The photo was captured at an angle, the affected area is the sole of the foot.
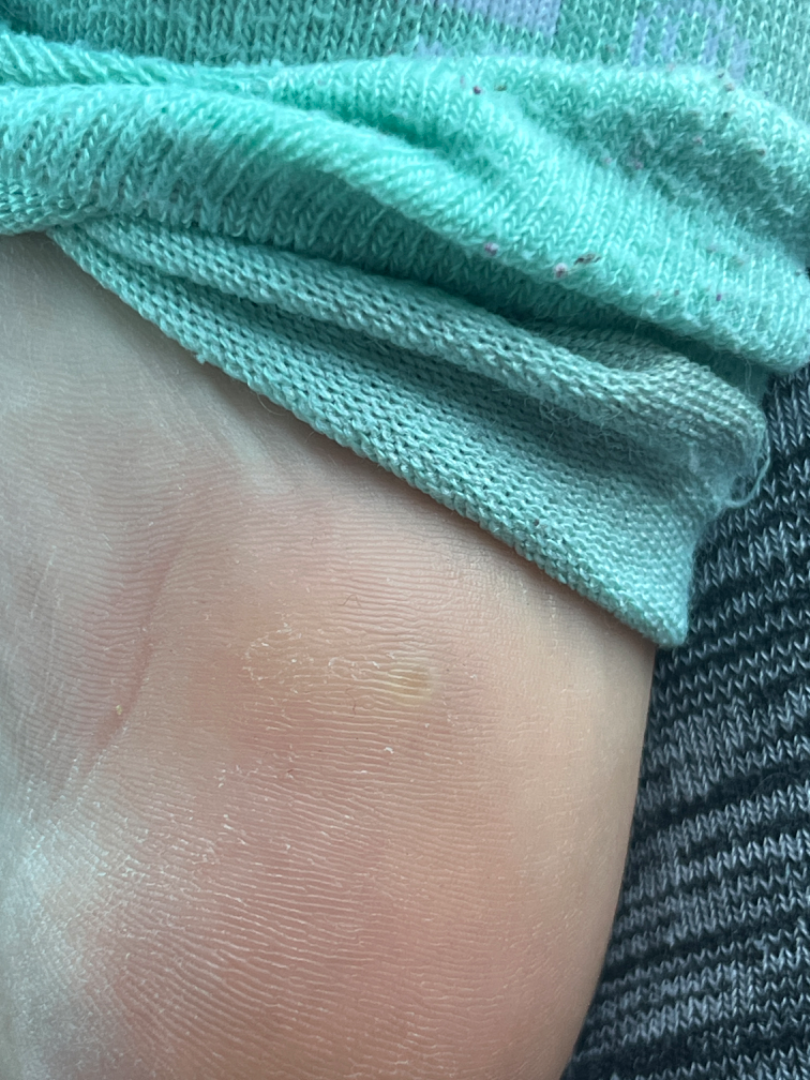Q: Reported symptoms?
A: pain
Q: What is the lesion texture?
A: raised or bumpy
Q: What conditions are considered?
A: the reviewer's impression was Verruca vulgaris